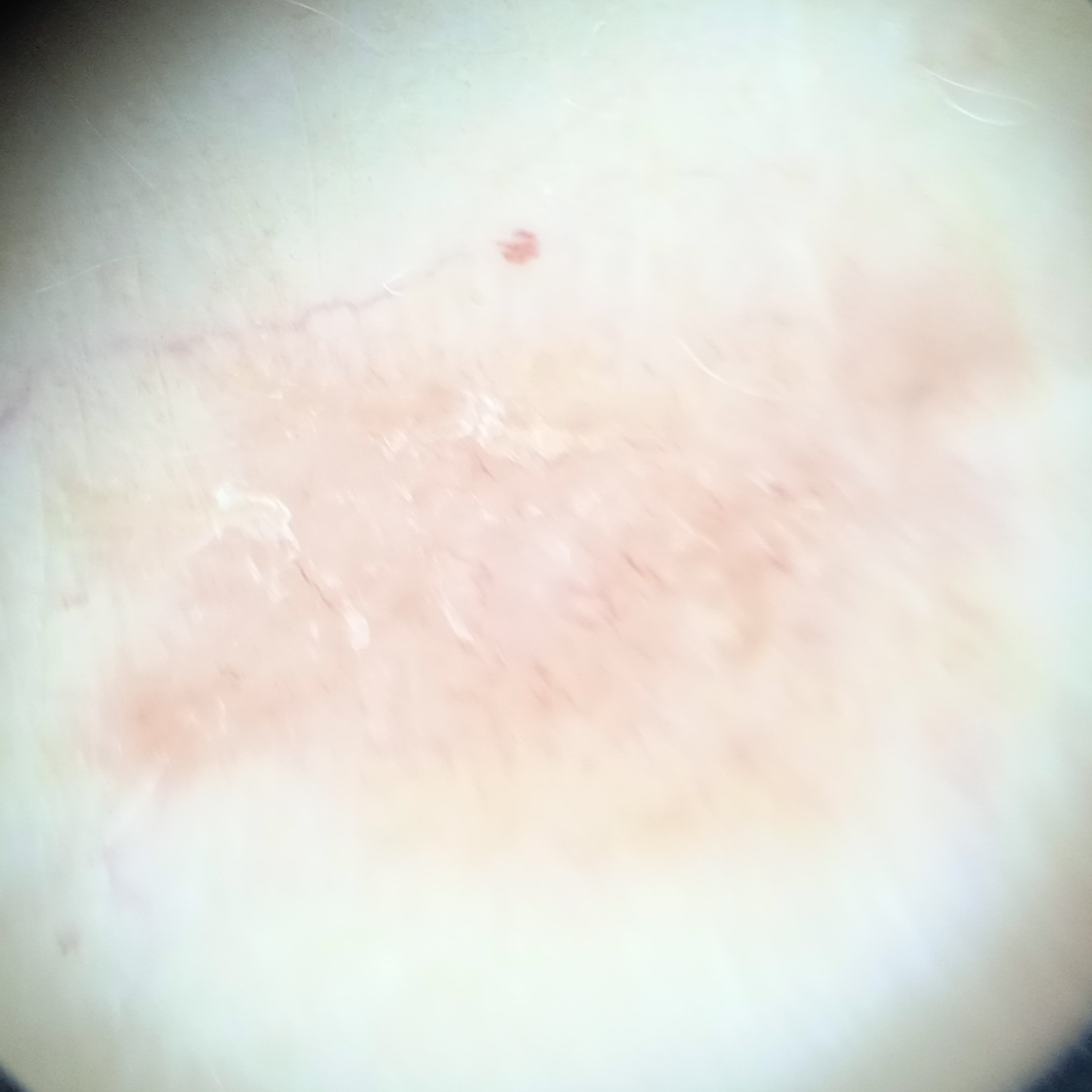diagnosis = basal cell carcinoma (biopsy-proven).